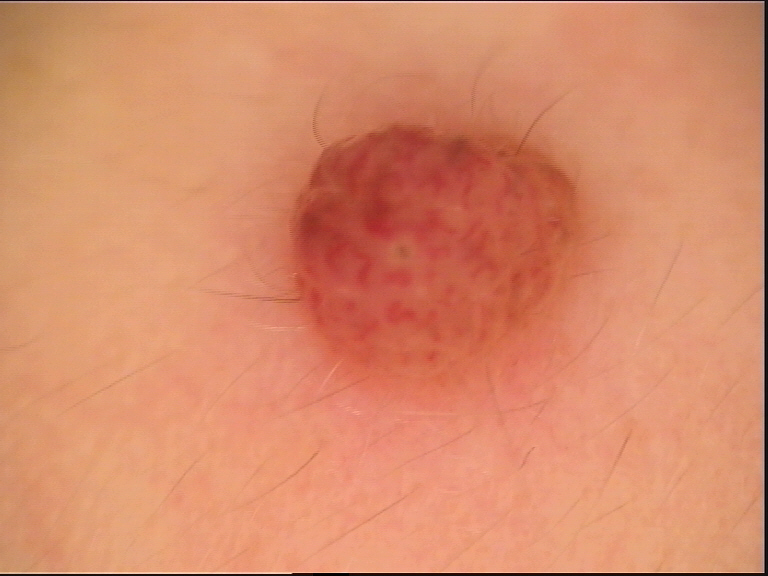image type: dermatoscopy; diagnosis: dermal nevus (expert consensus).